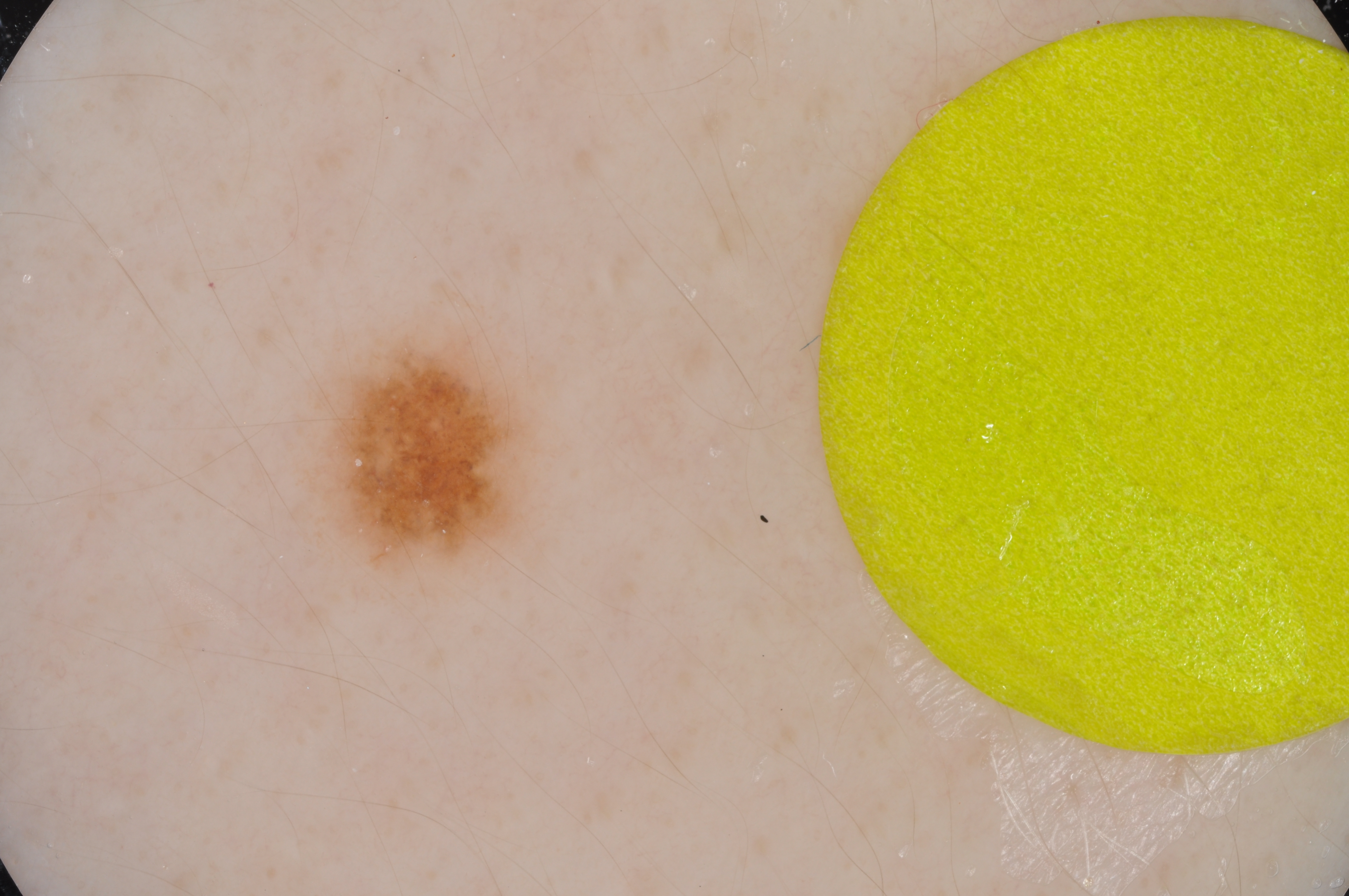{"image": {"modality": "dermoscopy"}, "lesion_location": {"bbox_xyxy": [307, 318, 546, 598]}, "diagnosis": {"name": "melanocytic nevus", "malignancy": "benign", "lineage": "melanocytic", "provenance": "clinical"}}